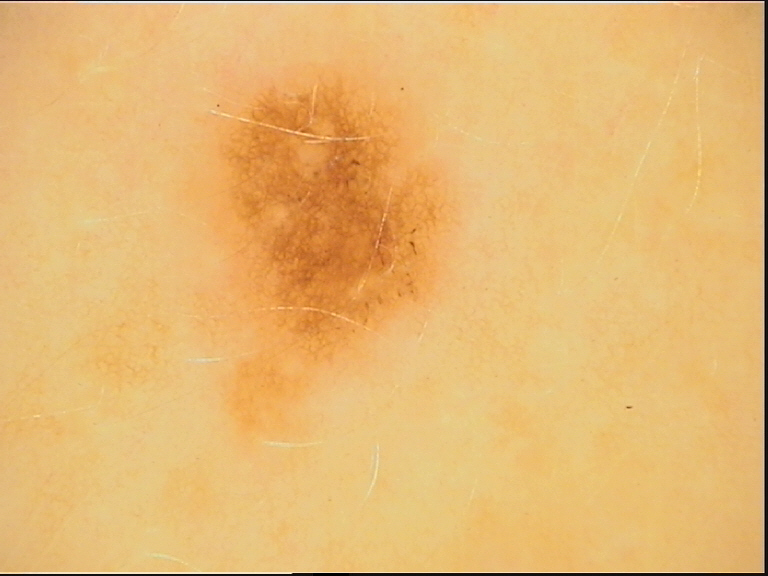The diagnostic label was a dysplastic junctional nevus.